Dermoscopy of a skin lesion.
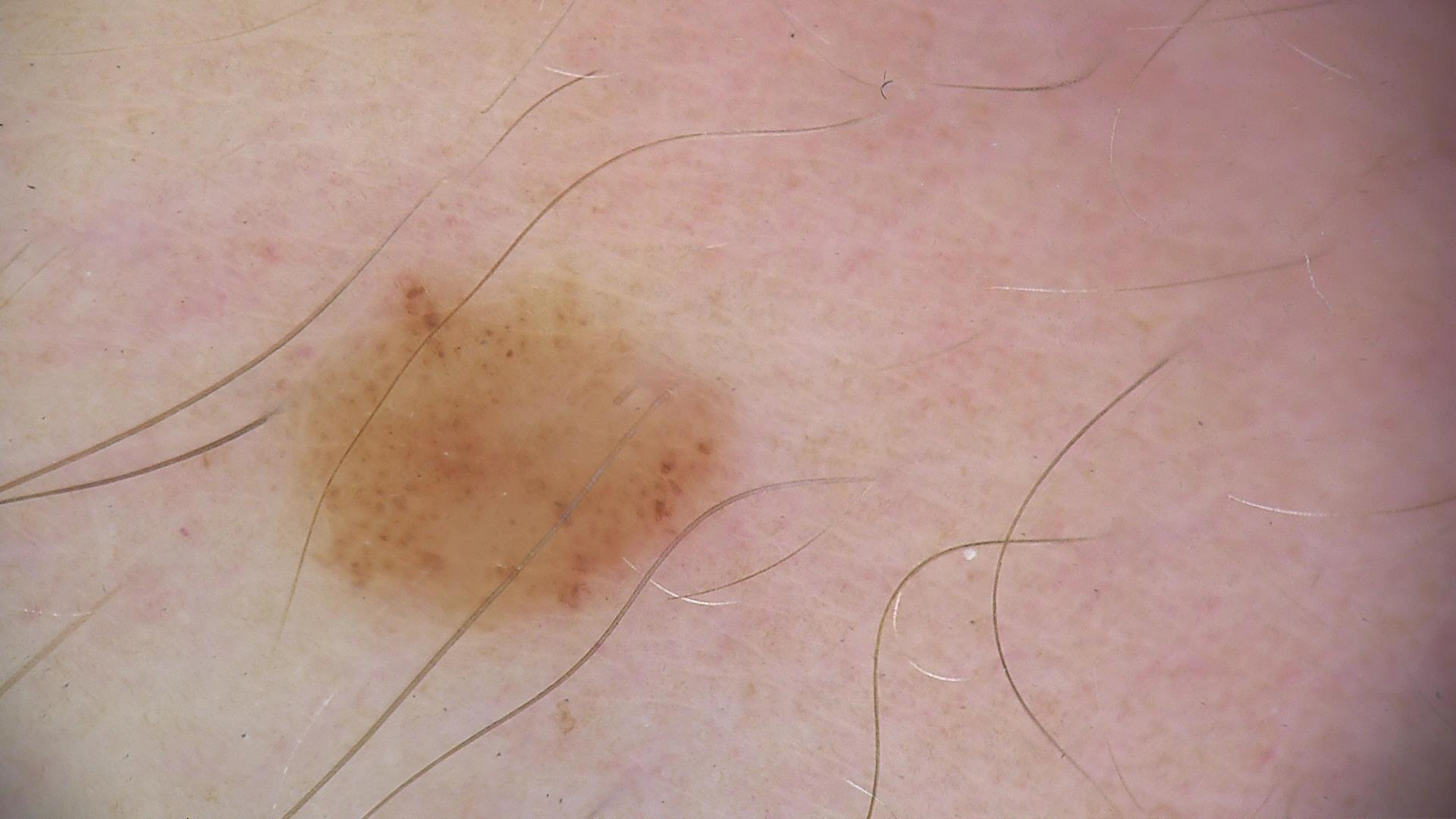{
  "diagnosis": {
    "name": "compound nevus",
    "code": "cb",
    "malignancy": "benign",
    "super_class": "melanocytic",
    "confirmation": "expert consensus"
  }
}